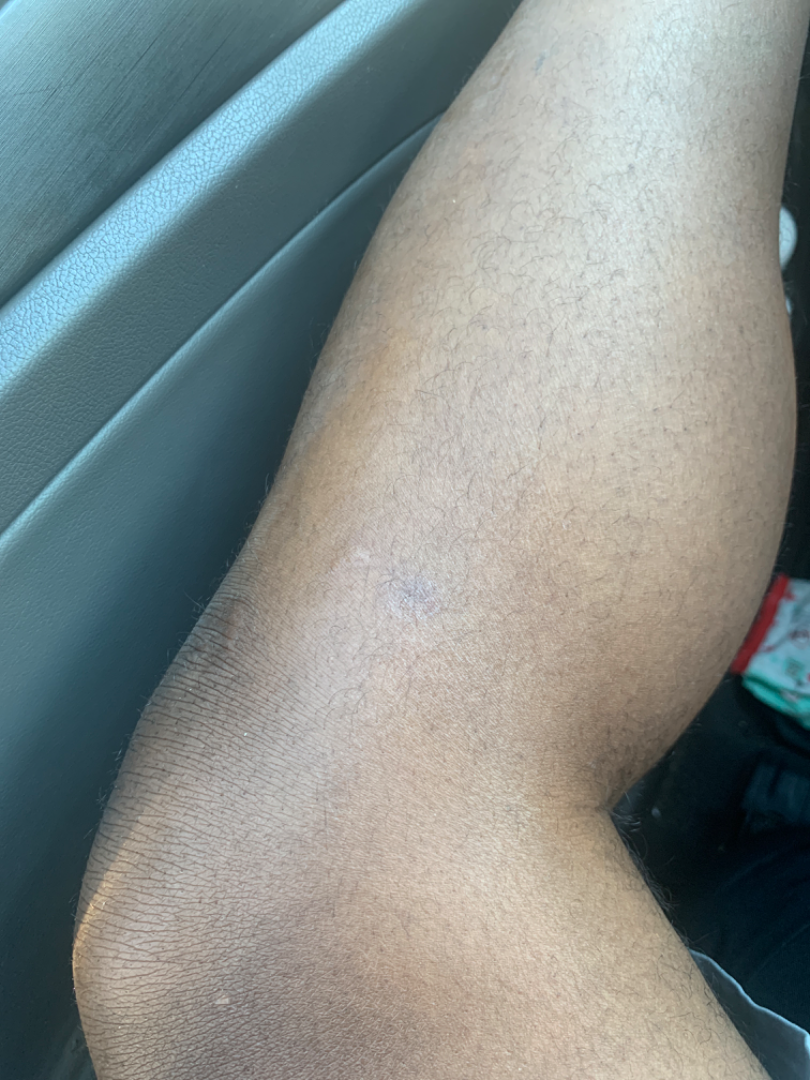Review: The skin findings could not be characterized from the image.